The photo was captured at a distance · the affected area is the arm and palm · the condition has been present for one to four weeks · the patient described the issue as a rash · the patient reported no systemic symptoms · texture is reported as rough or flaky · the patient notes itching · male contributor, age 18–29.
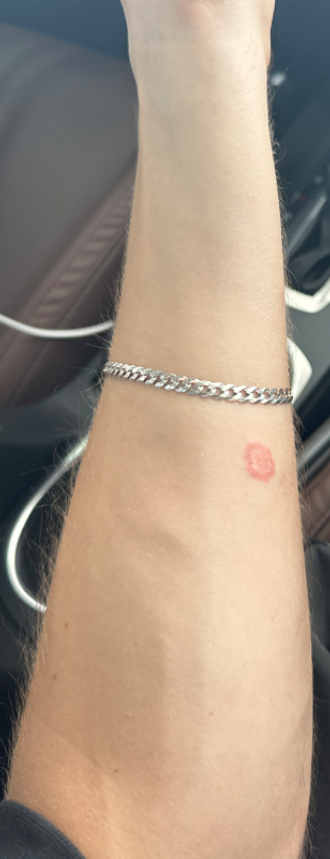The reviewing clinician's impression was: the differential, in no particular order, includes Tinea and Eczema; a more distant consideration is Psoriasis.